This is a close-up image.
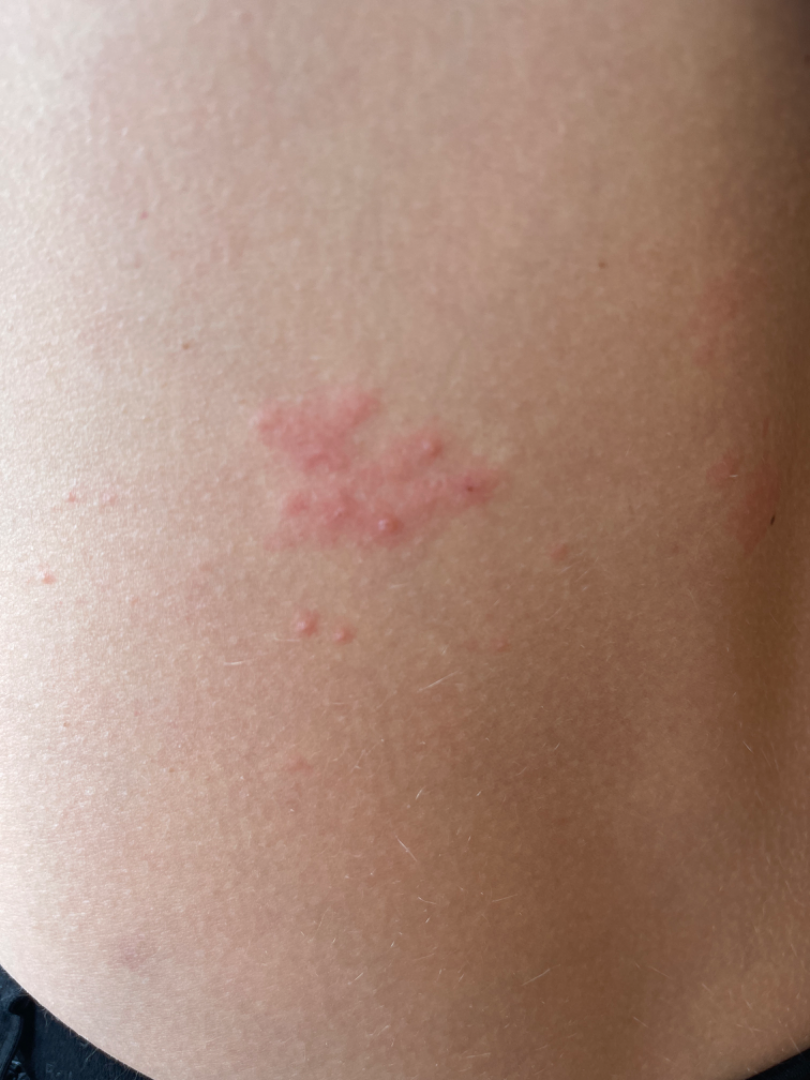Impression: The leading consideration is Herpes Simplex; the differential also includes Insect Bite; also consider Allergic Contact Dermatitis.